A dermoscopic view of a skin lesion.
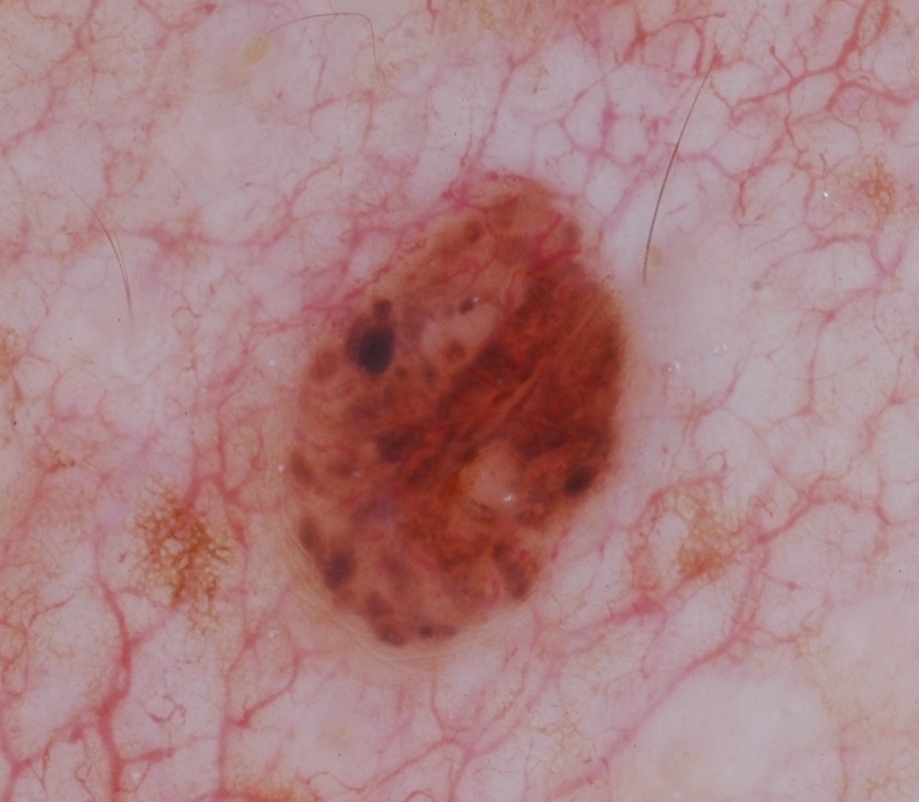Summary: The visible lesion spans x1=281, y1=175, x2=628, y2=646. Dermoscopic examination shows milia-like cysts and globules, with no streaks, pigment network, or negative network. The lesion occupies roughly 15% of the field. Impression: The lesion was assessed as a melanocytic nevus.